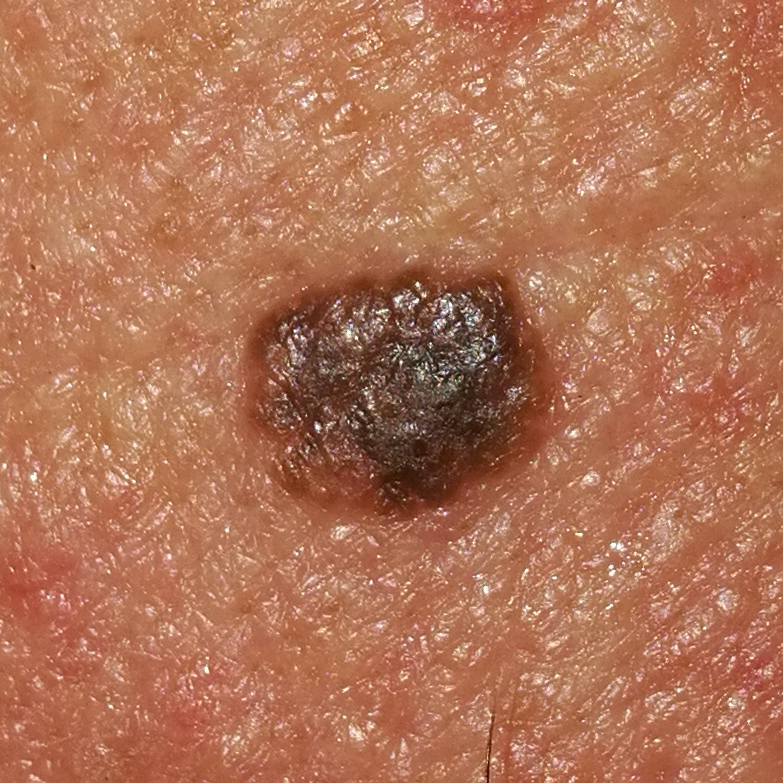* subject: 41 years old
* imaging: smartphone clinical photo
* site: the face
* symptoms: elevation, growth
* impression: nevus (clinical consensus)